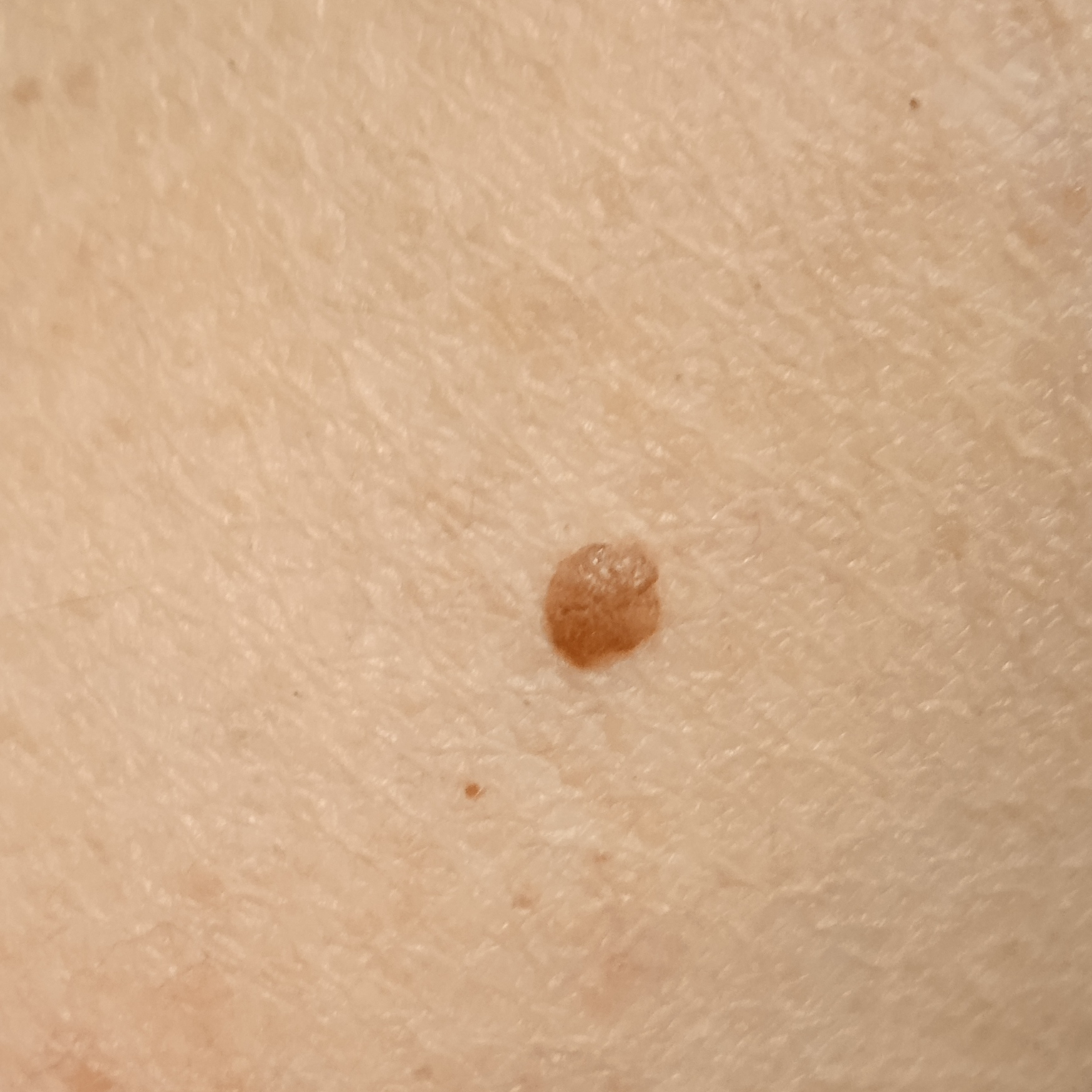– patient: male, 65 years of age
– risk factors: immunosuppression, a family history of skin cancer, a personal history of skin cancer
– sun reaction: skin reddens painfully with sun exposure
– nevus count: numerous melanocytic nevi
– referral: research study (no referral diagnosis)
– location: an arm
– lesion size: 3 mm
– diagnosis: melanocytic nevus (dermatologist consensus)